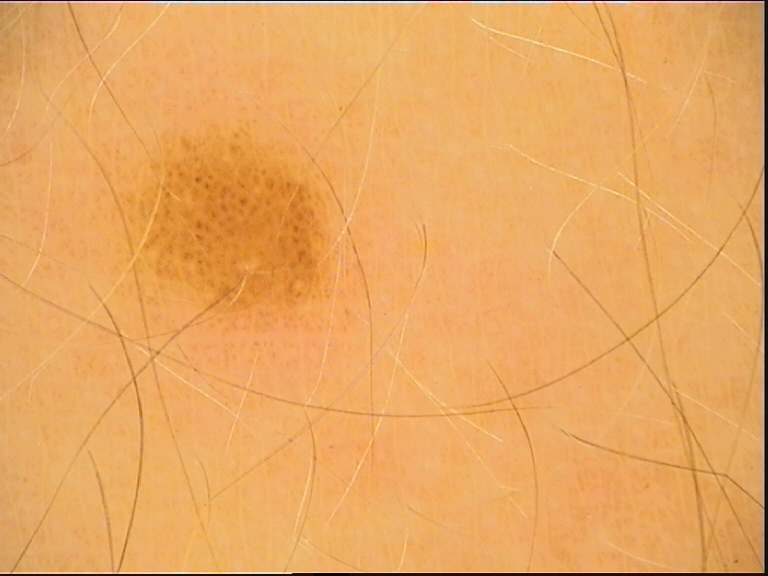A skin lesion imaged with a dermatoscope.
Consistent with a benign lesion — a dysplastic junctional nevus.